A female patient roughly 25 years of age · a dermoscopy image of a single skin lesion.
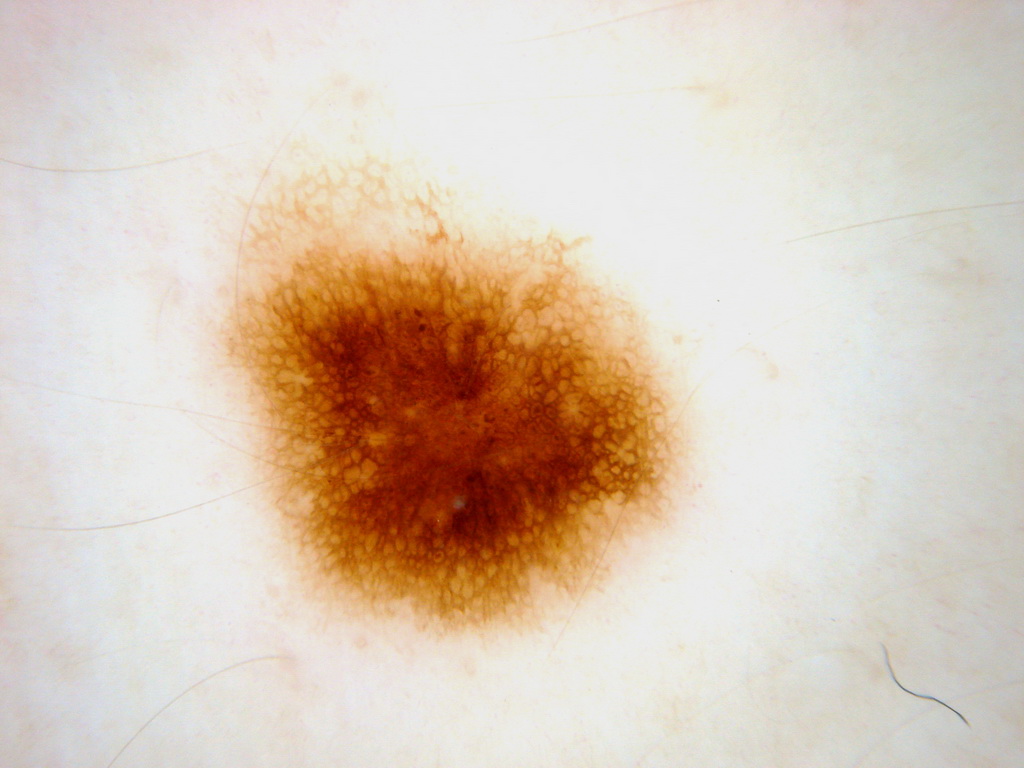Dermoscopy demonstrates pigment network and globules; no streaks, milia-like cysts, or negative network. In (x1, y1, x2, y2) order, the lesion is bounded by 206 156 691 647. Diagnosed as a melanocytic nevus, a benign lesion.